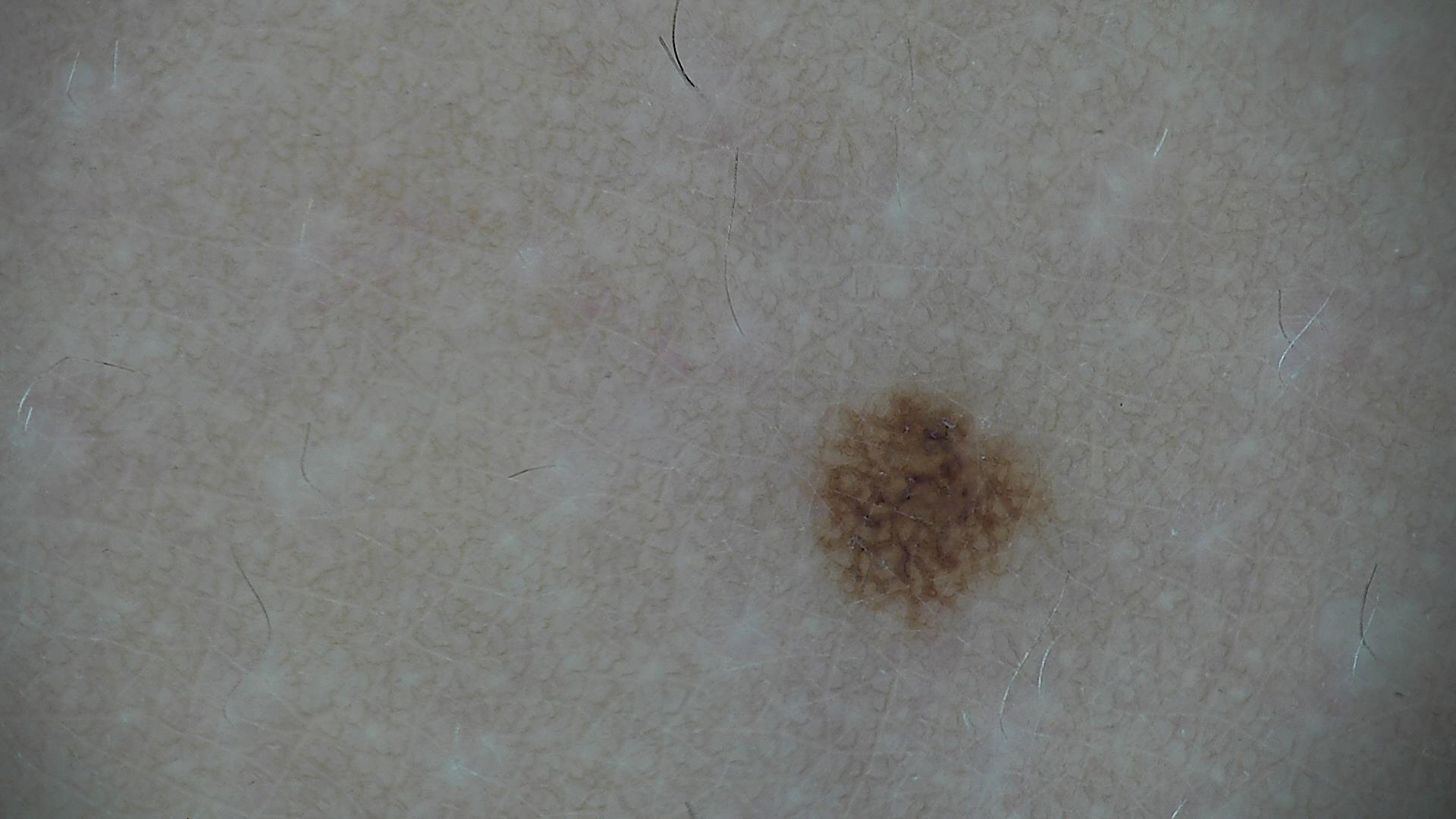* diagnostic label · dysplastic junctional nevus (expert consensus)